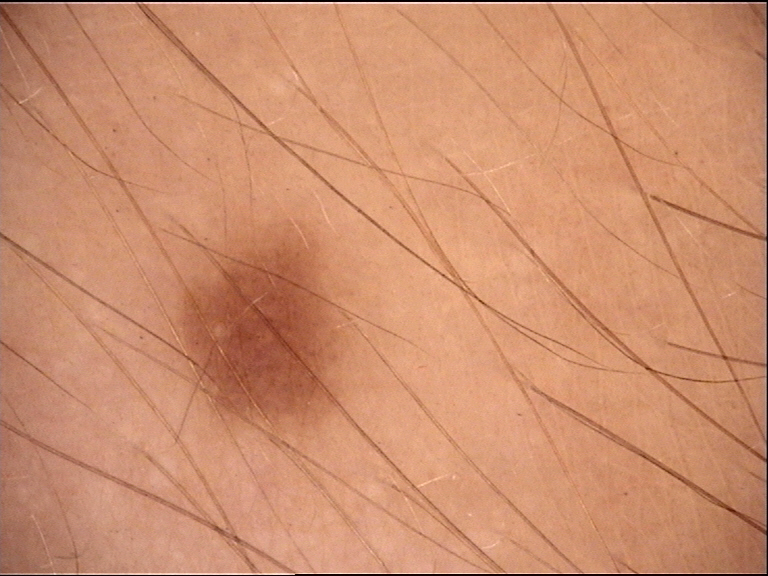Consistent with a junctional nevus.